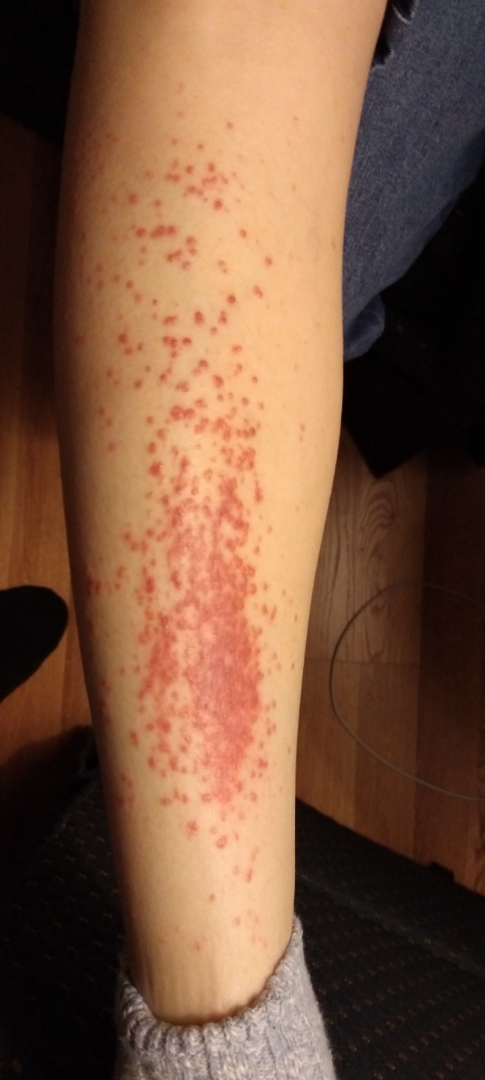image framing = close-up
diagnostic considerations = single-reviewer assessment: the primary impression is Lichen planus/lichenoid eruption; also on the differential is Amyloidosis of skin; an alternative is Eczema